Close-up view · the affected area is the back of the hand and arm — 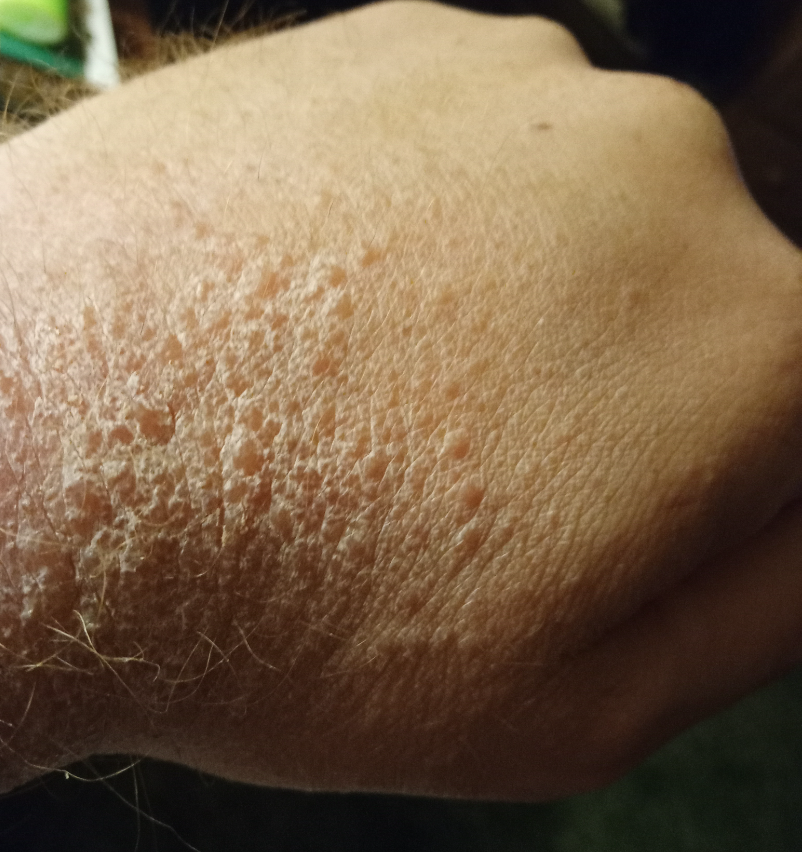  differential:
    tied_lead:
      - Impetigo
      - Lichen Simplex Chronicus
      - Allergic Contact Dermatitis